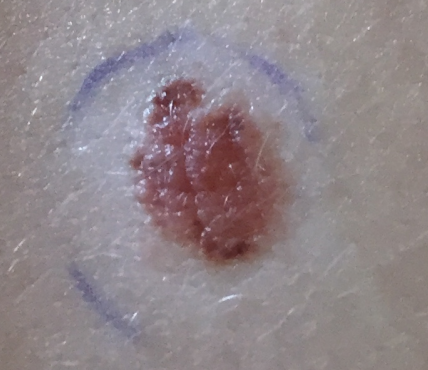patient=20 years old; modality=clinical photograph; reported symptoms=elevation / no itching; diagnosis=nevus (clinical consensus).